A clinical photograph of a skin lesion; the patient says their skin reddens painfully with sun exposure; a female subject aged 35.
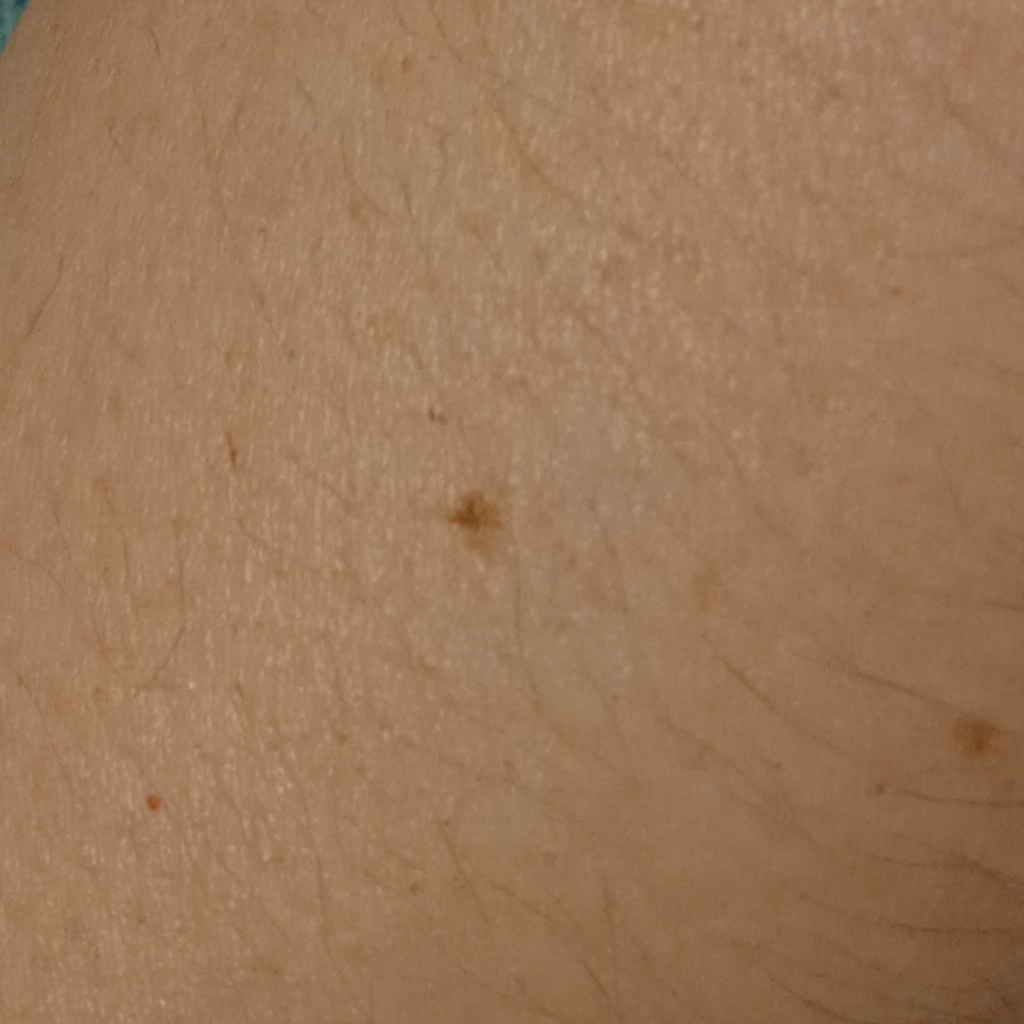Located on an arm. Measuring roughly 2.1 mm. The diagnostic impression was a melanocytic nevus.